The patient considered this a rash; the photo was captured at an angle; skin tone: human graders estimated MST 2 (US pool) or 3 (India pool); the contributor reports the lesion is raised or bumpy; no associated systemic symptoms reported; the condition has been present for less than one week; the lesion is associated with itching, bothersome appearance and burning — 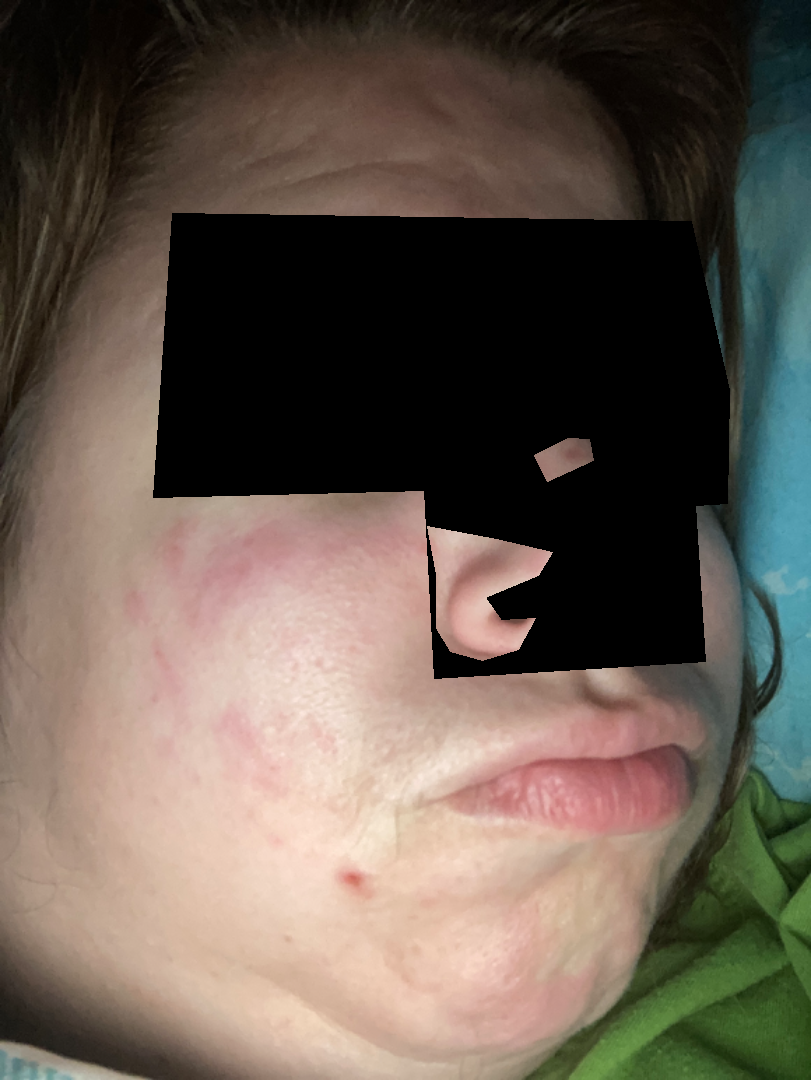On photographic review: the leading consideration is Rosacea; an alternative is Allergic Contact Dermatitis; possibly Cutaneous lupus.